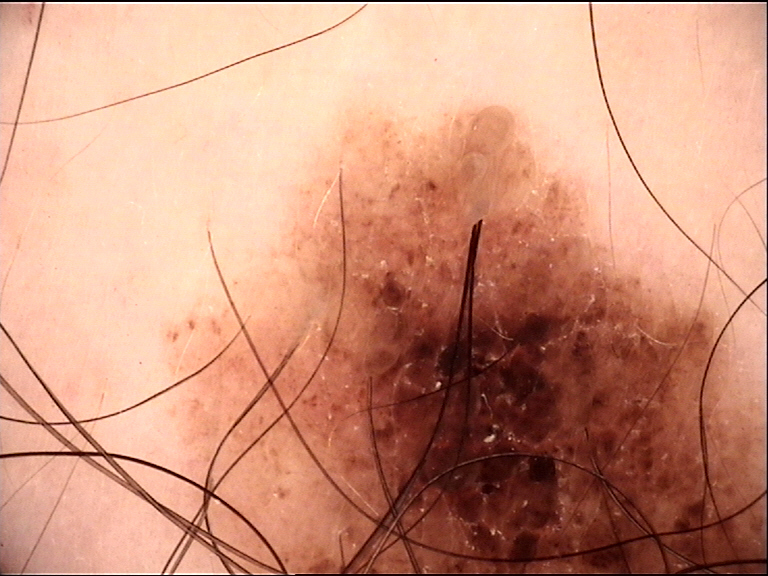lesion type=banal | assessment=compound nevus (expert consensus).